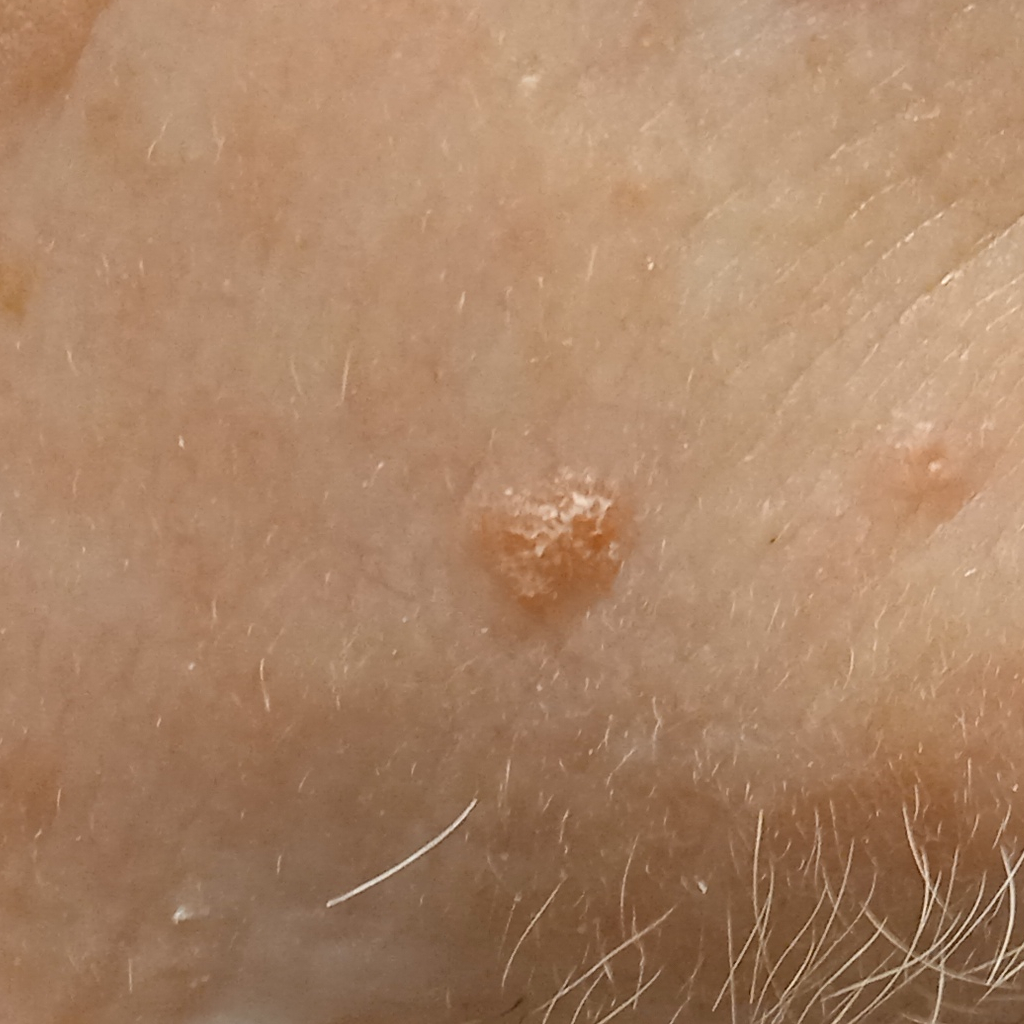Q: What are the relevant risk factors?
A: a personal history of cancer, a personal history of skin cancer, no family history of skin cancer, no prior organ transplant
Q: Patient demographics?
A: male, age 77
Q: What is the imaging modality?
A: clinical photograph
Q: What is the patient's nevus burden?
A: a moderate number of melanocytic nevi
Q: What is the anatomic site?
A: the face
Q: Lesion size?
A: 4.3 mm
Q: What was the diagnosis?
A: actinic keratosis (dermatologist consensus)